A male subject, aged 68 to 72 · a dermoscopy image of a single skin lesion — 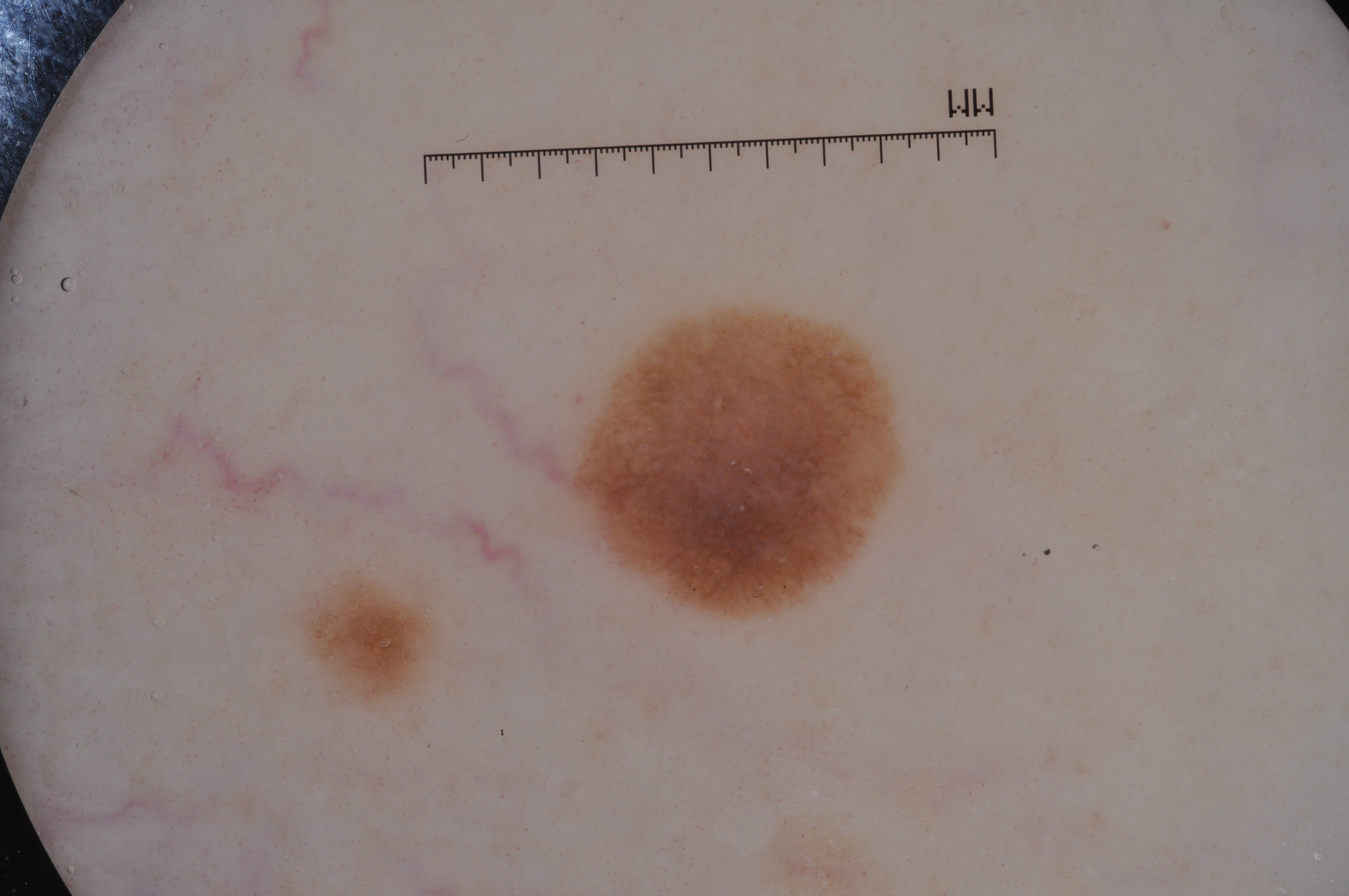dermoscopic findings = pigment network and milia-like cysts; absent: streaks and negative network
lesion bbox = x1=569, y1=309, x2=896, y2=616
size = small
assessment = a melanocytic nevus, a benign lesion